A dermatoscopic image of a skin lesion · a female subject aged around 45.
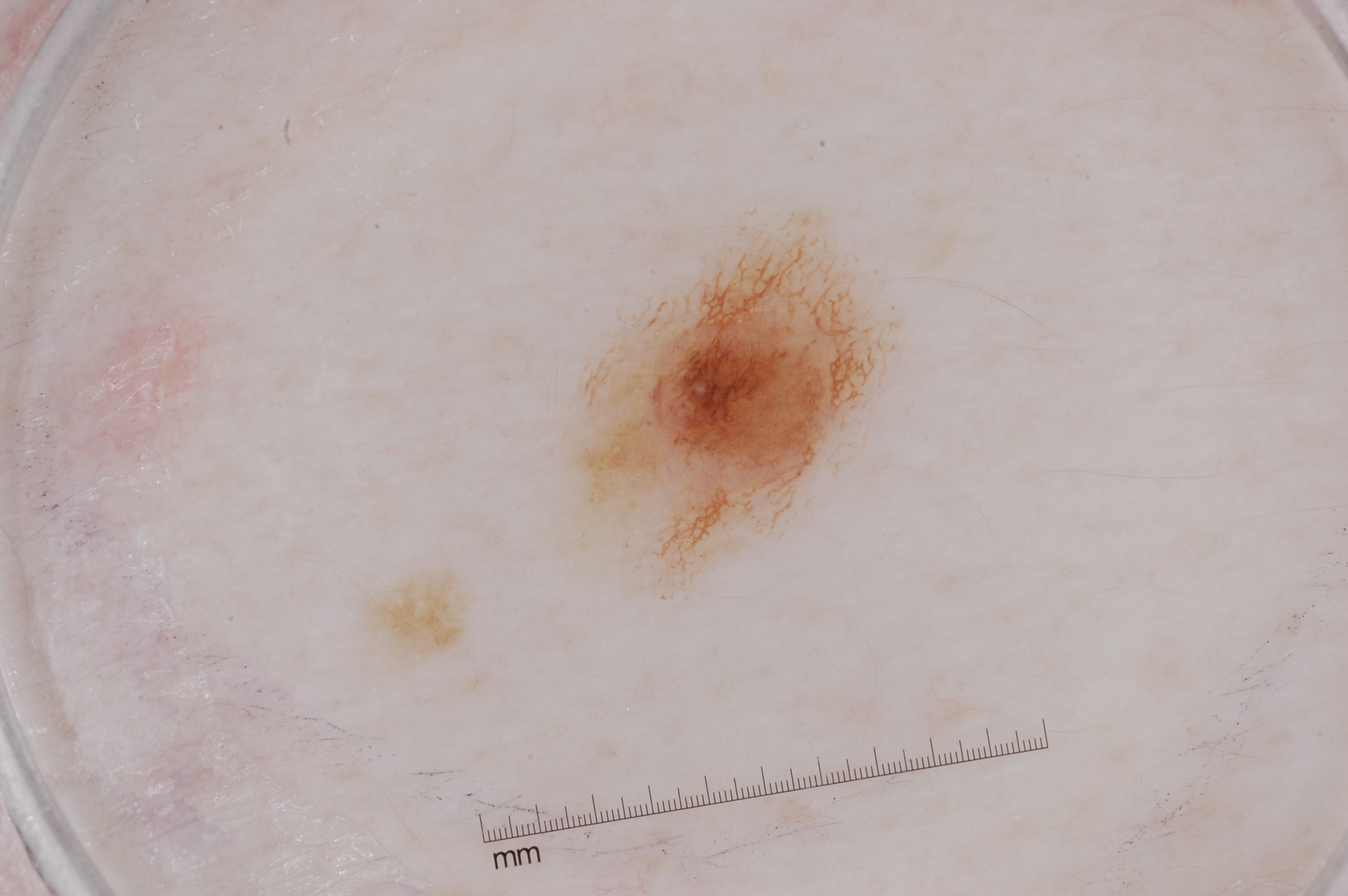As (left, top, right, bottom), the lesion spans 555 205 903 599.
Dermoscopic review identifies pigment network, with no streaks, negative network, or milia-like cysts.
The diagnostic assessment was a melanocytic nevus.